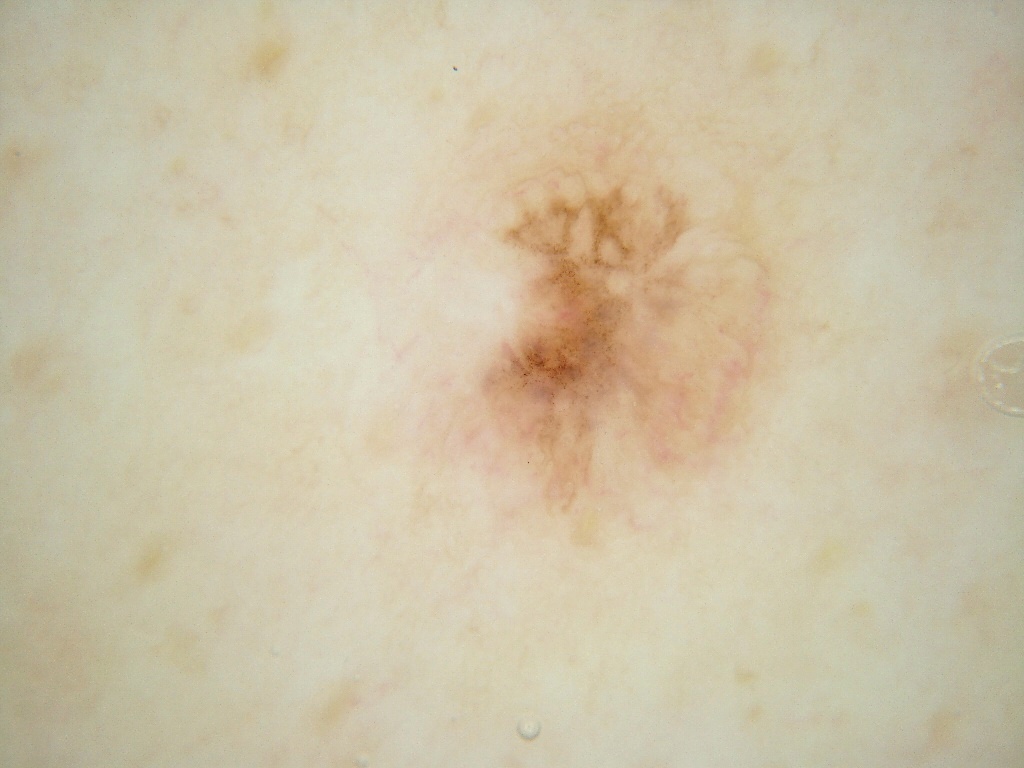A dermoscopic image of a skin lesion.
The lesion spans bbox(446, 116, 794, 559).
On dermoscopy, the lesion shows no streaks or globules.
The lesion occupies roughly 15% of the field.
Clinically diagnosed as a benign skin lesion.